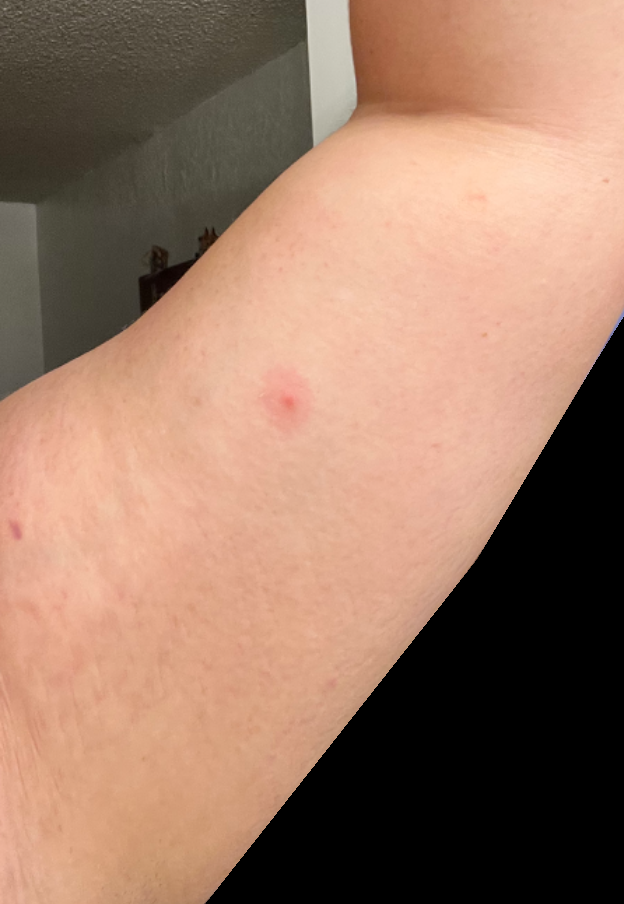The lesion is associated with itching.
Close-up view.
The patient reports the condition has been present for less than one week.
The affected area is the arm.
The patient reports the lesion is raised or bumpy.
On photographic review, Insect Bite (leading).